A male patient 68 years old; the patient is Fitzpatrick skin type II; a clinical photo of a skin lesion taken with a smartphone: 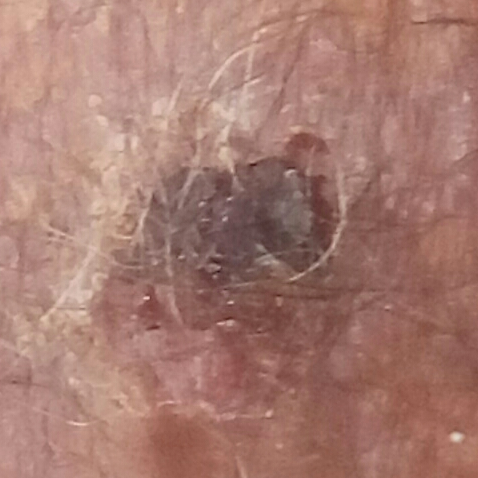The lesion is on a forearm. The lesion measures approximately 11 × 8 mm. The patient reports that the lesion itches, has grown, is elevated, and has bled, but has not changed. Histopathological examination showed a skin cancer — a basal cell carcinoma.